Reported duration is less than one week; this image was taken at an angle; female subject, age 18–29 — 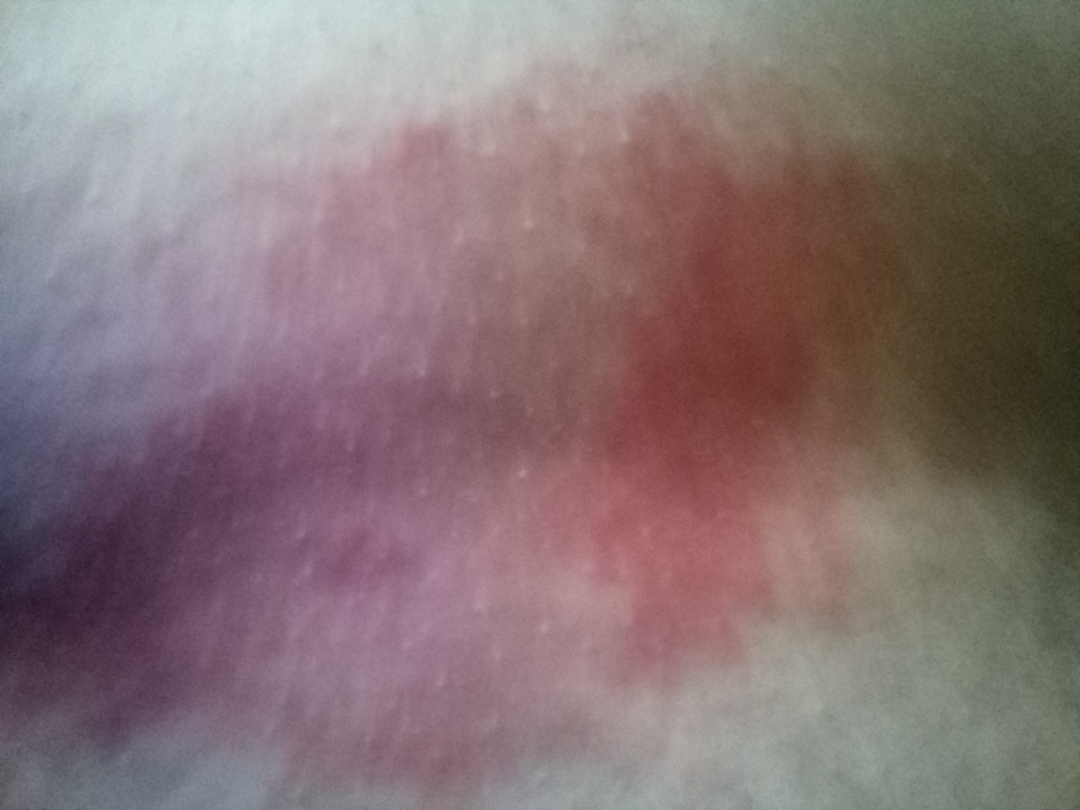Findings:
Inverse psoriasis, Candida intertrigo and Seborrheic Dermatitis were considered with similar weight.